This image was taken at a distance:
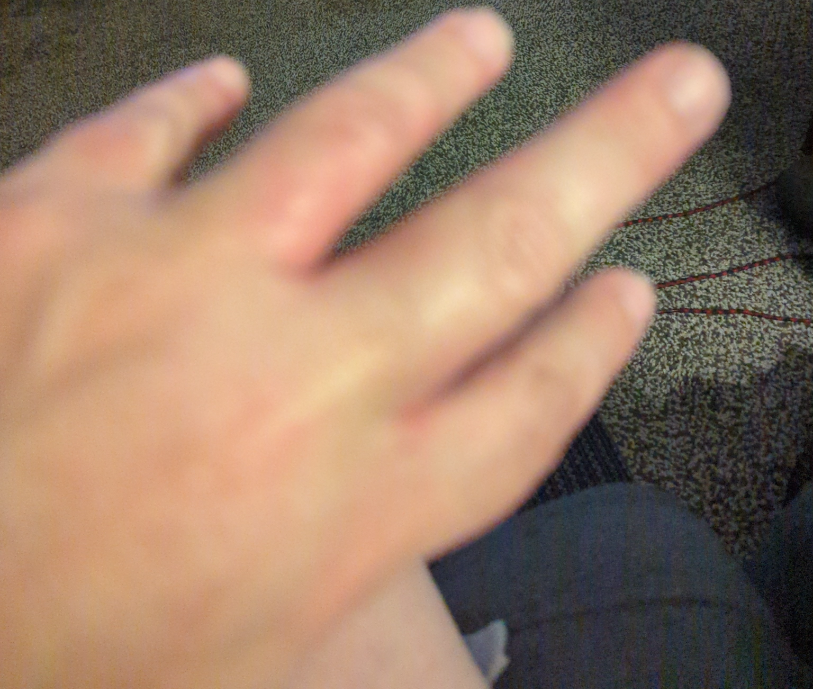Notes:
* diagnostic considerations · in keeping with Eczema